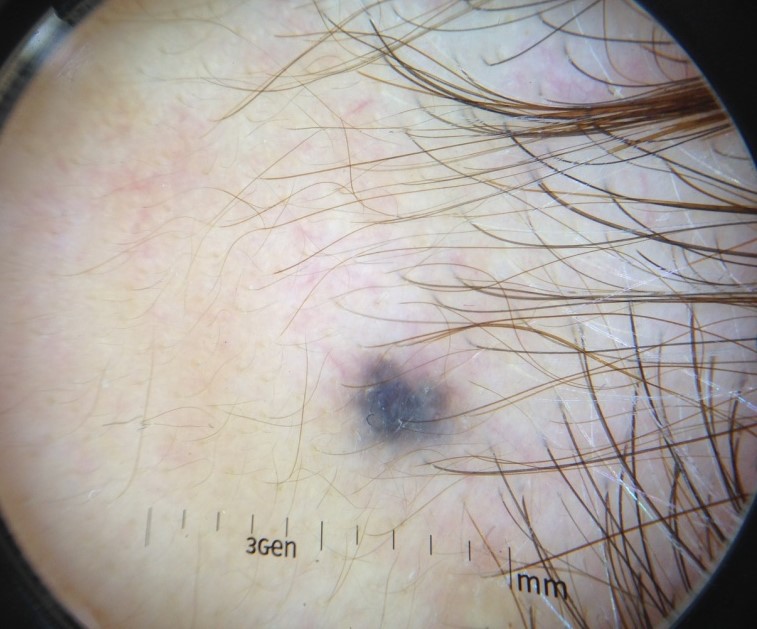Labeled as a banal lesion — a blue nevus.